A dermoscopic close-up of a skin lesion: 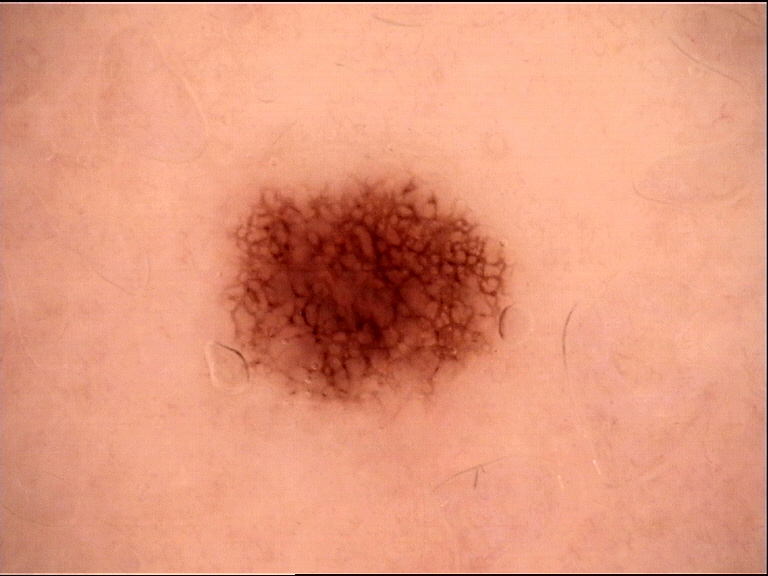Conclusion:
Consistent with a dysplastic junctional nevus.